Dermoscopy of a skin lesion:
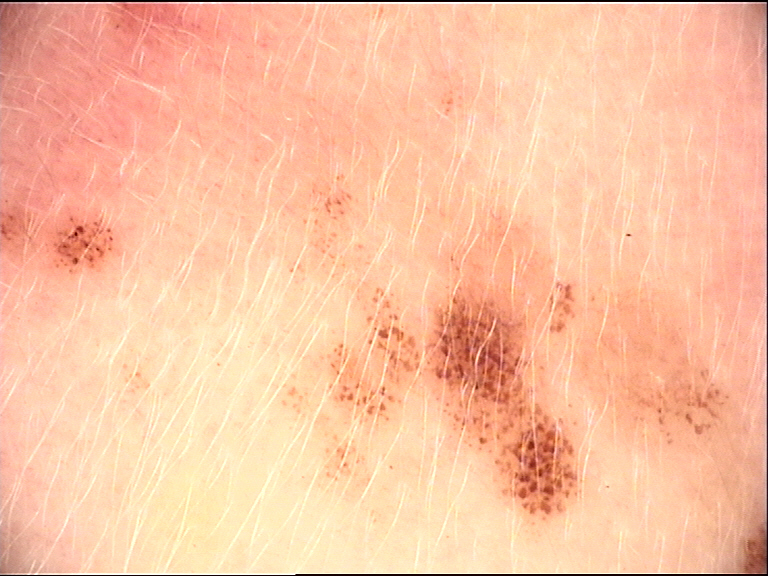Impression: The diagnosis was a banal lesion — a congenital junctional nevus.